The patient also reports mouth sores. Reported duration is about one day. Symptoms reported: bothersome appearance. The contributor is 40–49, female. The lesion involves the head or neck. Texture is reported as raised or bumpy. The photo was captured at a distance:
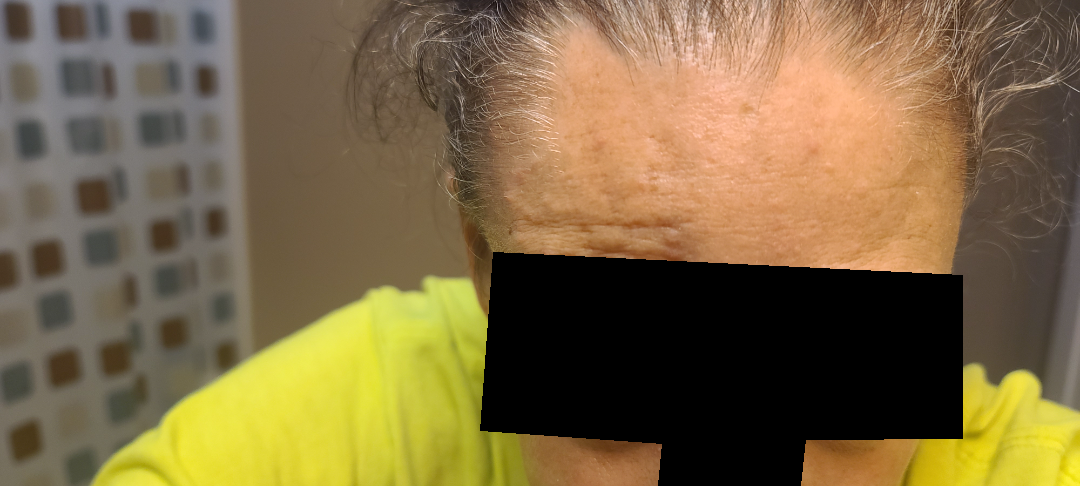Assessment:
No differential diagnosis could be assigned on photographic review.